Dermoscopy of a skin lesion; a female patient aged around 50:
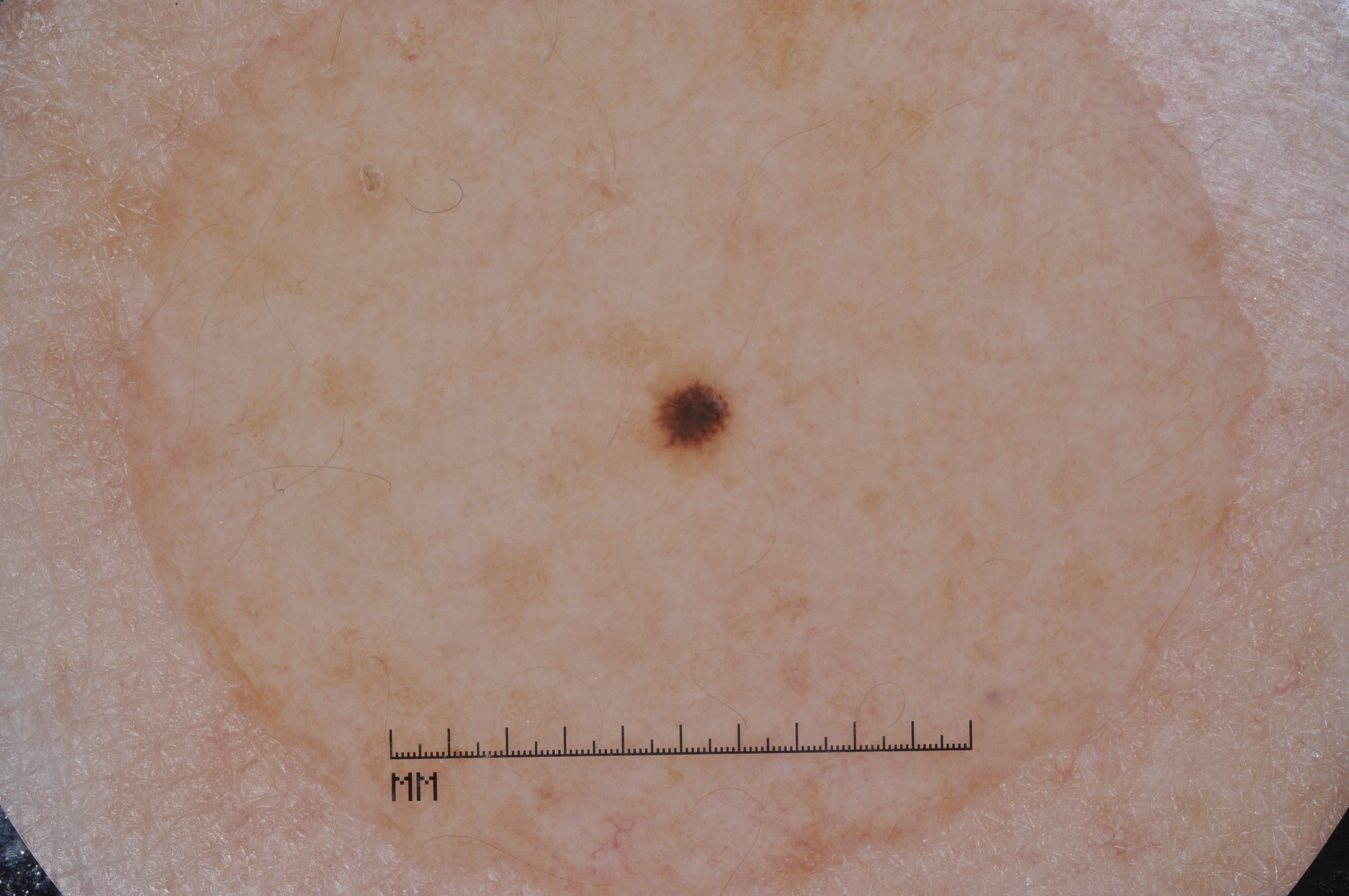dermoscopic_features:
  present:
    - streaks
    - pigment network
  absent:
    - milia-like cysts
    - negative network
lesion_extent: small
lesion_location:
  bbox_xyxy:
    - 643
    - 371
    - 727
    - 462
diagnosis:
  name: melanocytic nevus
  malignancy: benign
  lineage: melanocytic
  provenance: clinical